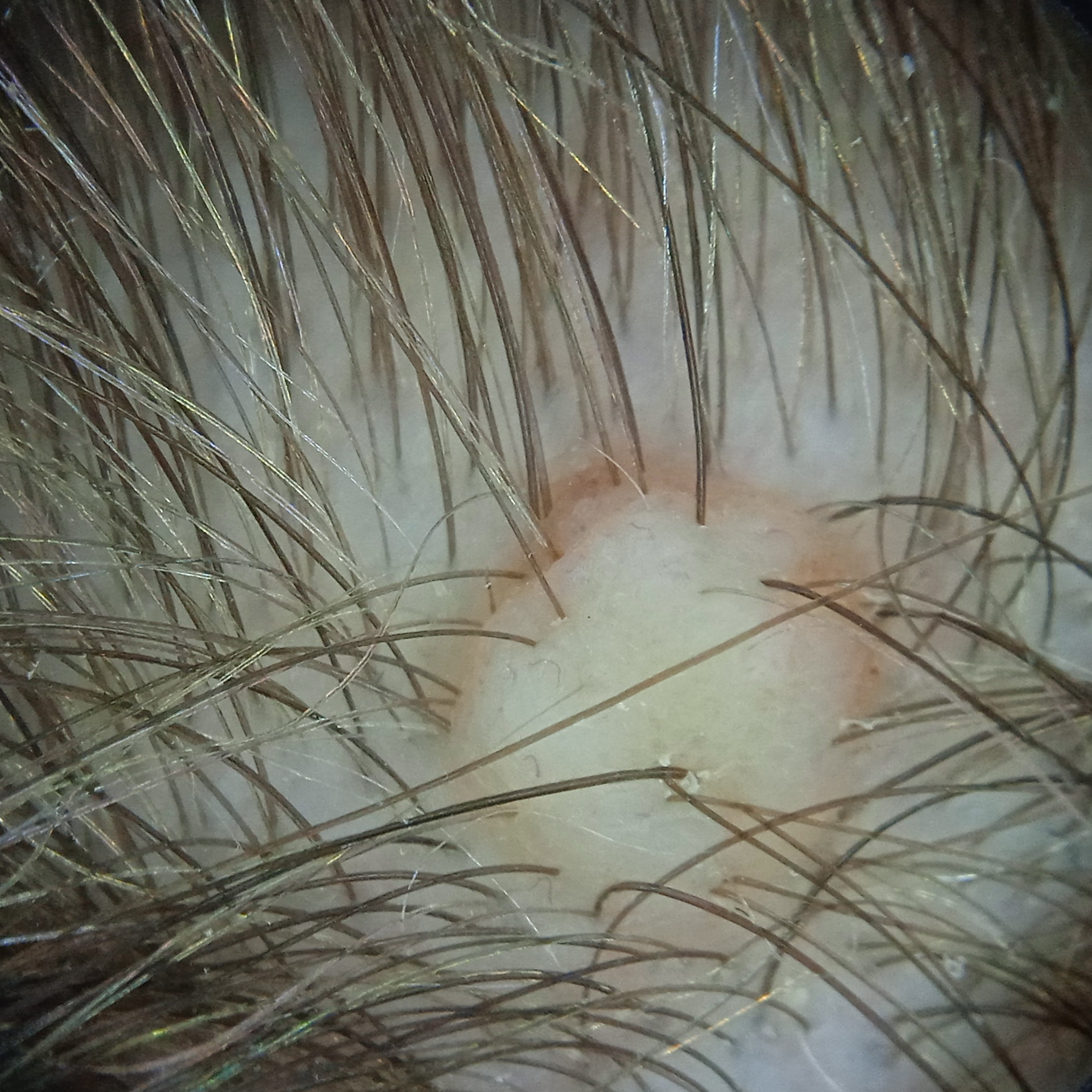Diagnosis: Histopathologically confirmed as a melanocytic nevus, following excision.